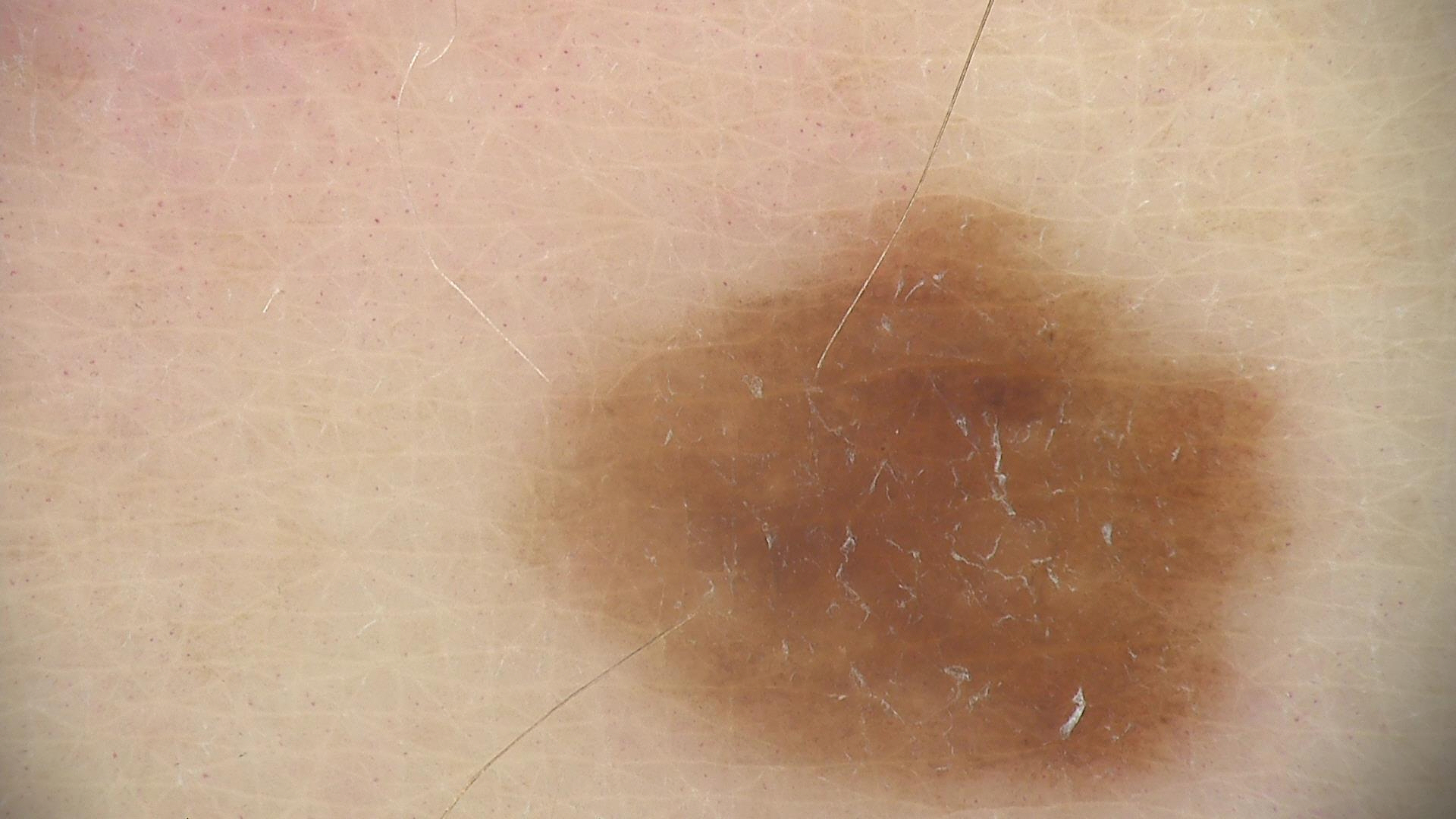Q: What is the imaging modality?
A: dermatoscopy
Q: What was the diagnostic impression?
A: dysplastic junctional nevus (expert consensus)